The photo was captured at an angle; the contributor reports the condition has been present for more than one year; texture is reported as raised or bumpy and rough or flaky; Fitzpatrick skin type V:
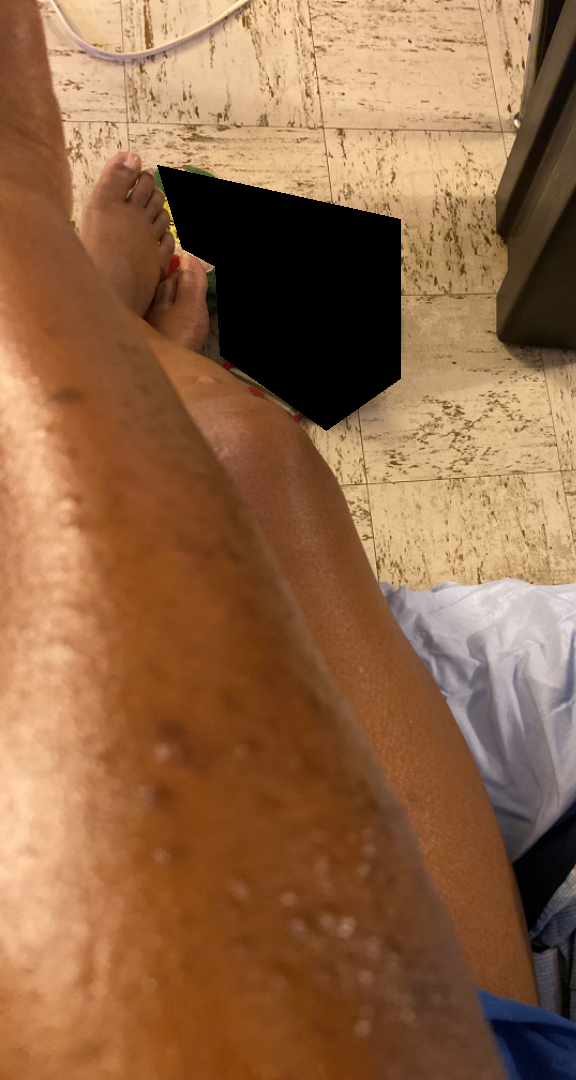assessment = unable to determine.